A dermoscopic photograph of a skin lesion:
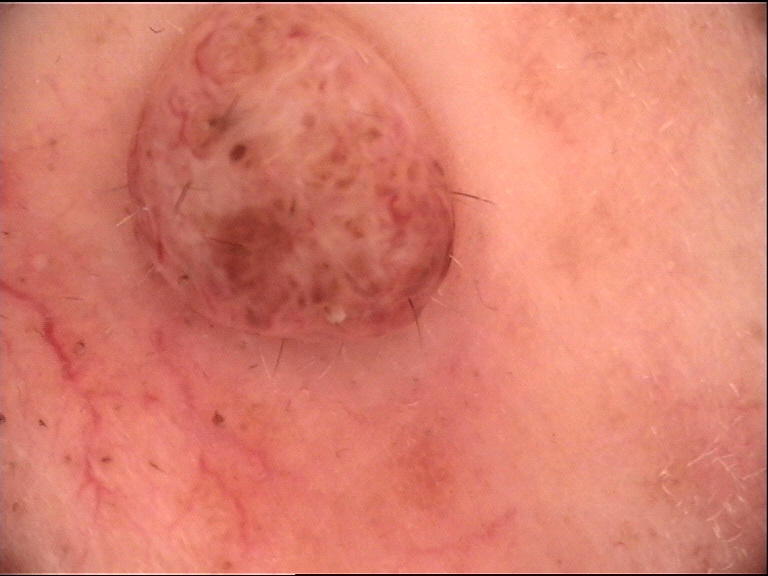The architecture is that of a banal lesion. The diagnosis was a dermal nevus.